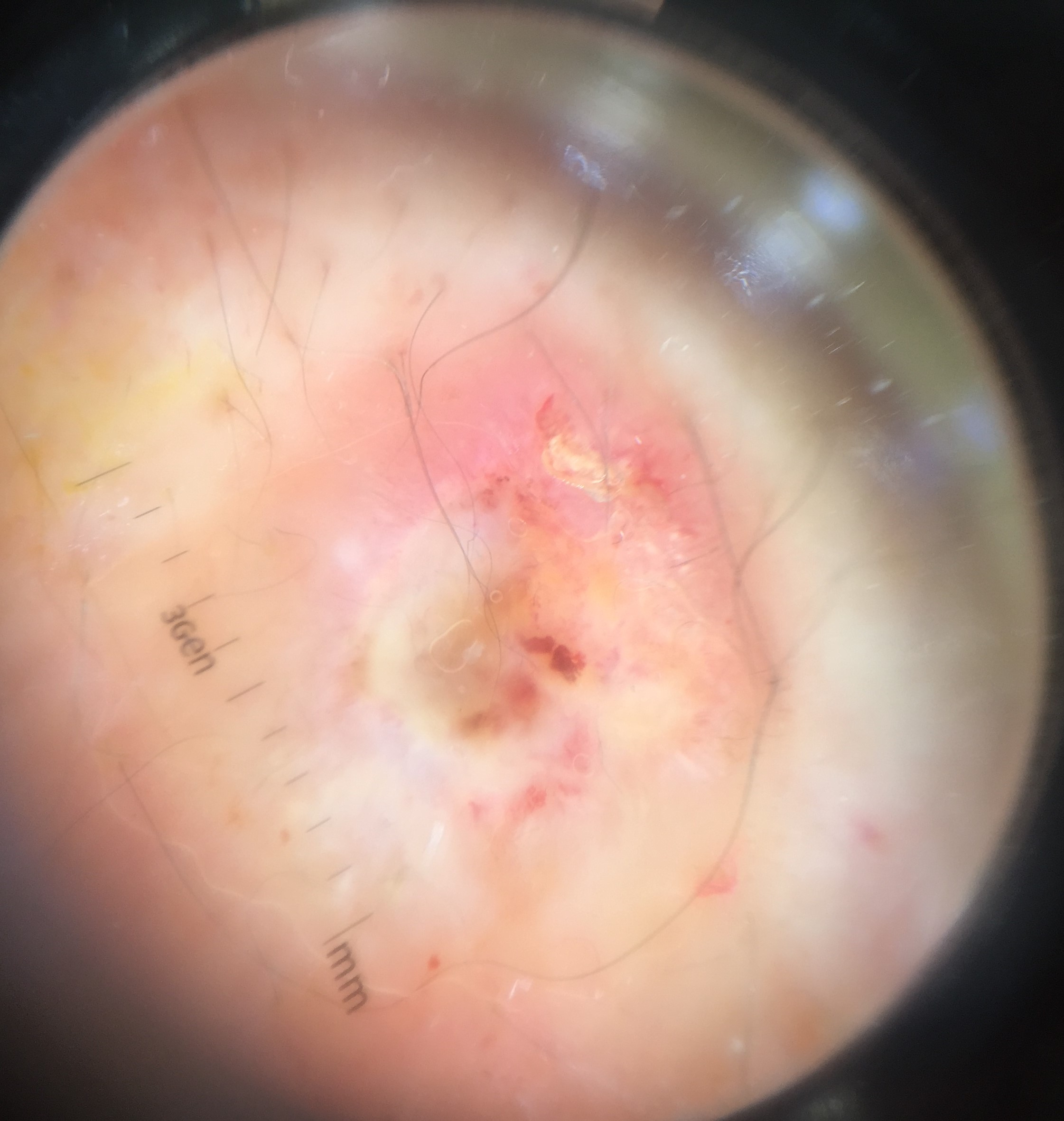Confirmed on histopathology as a squamous cell carcinoma.